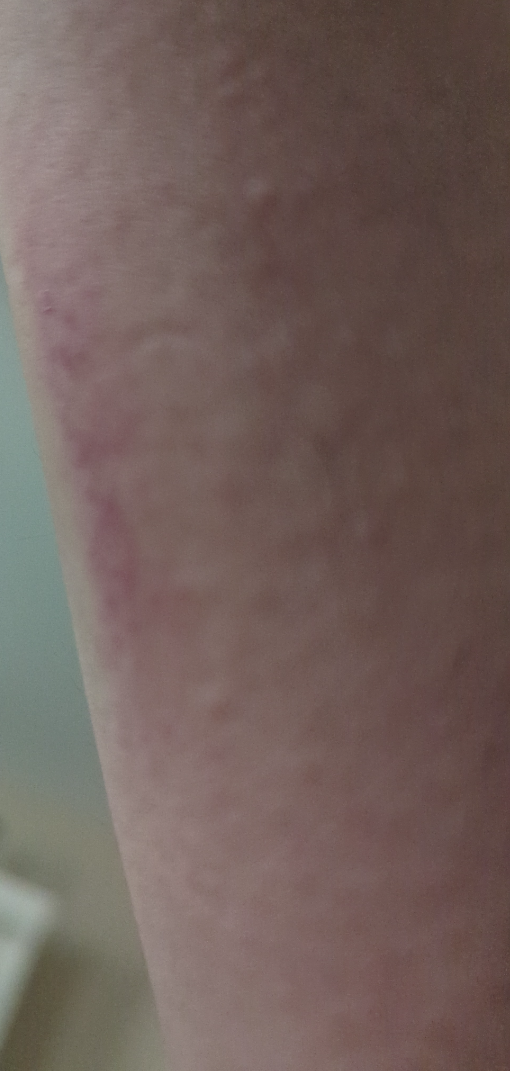The patient indicates the condition has been present for about one day. Located on the arm. An image taken at an angle. The patient indicates the lesion is raised or bumpy. Male contributor, age 18–29. Self-categorized by the patient as a rash. Symptoms reported: itching. No relevant systemic symptoms. On independent review by the dermatologists: the differential includes Irritant Contact Dermatitis; Abrasion, scrape, or scab; Contact dermatitis; and Eczema, with no clear leading consideration; less probable is Allergic Contact Dermatitis.